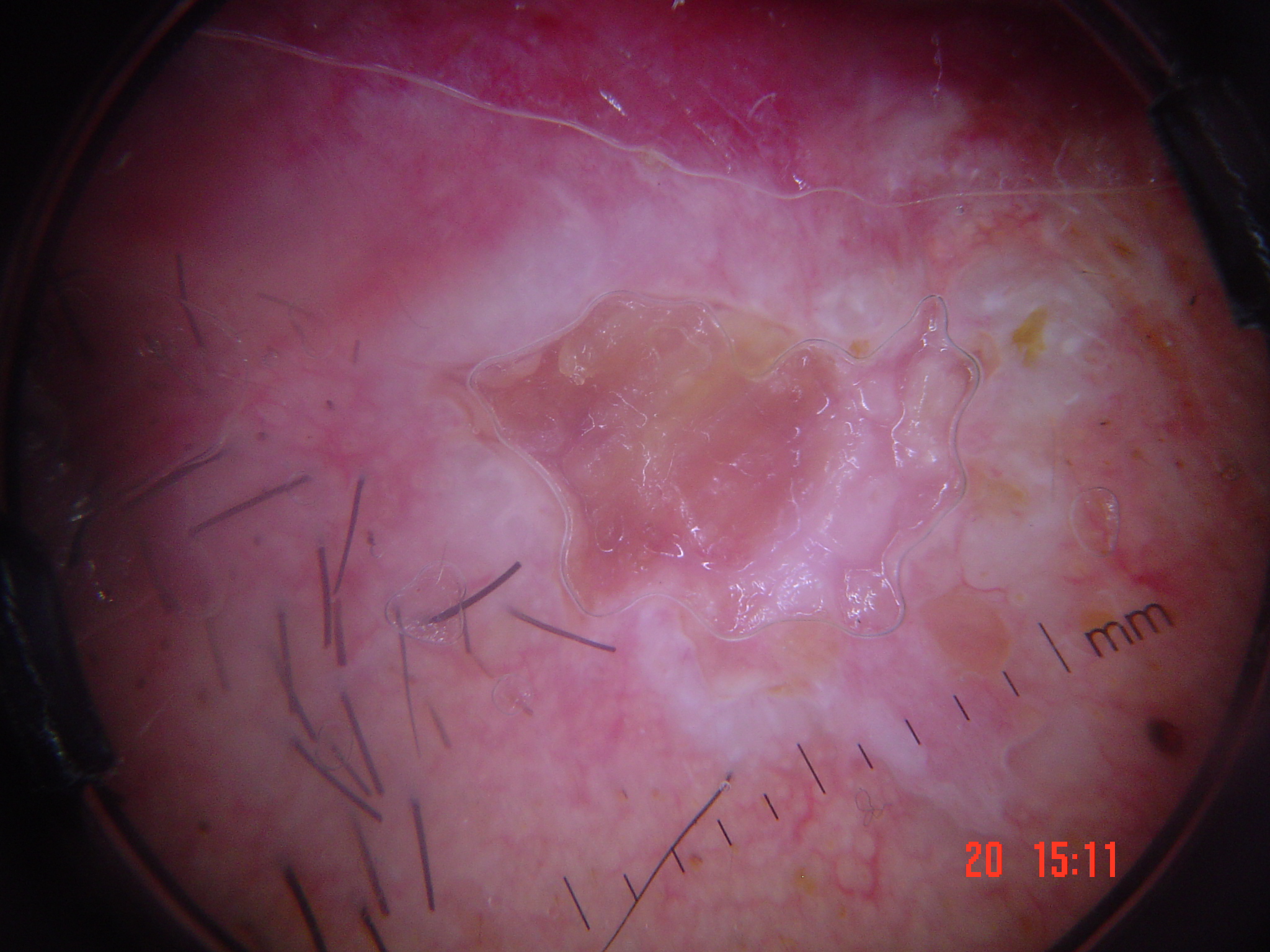A dermoscopic close-up of a skin lesion. The architecture is that of a keratinocytic lesion. The biopsy diagnosis was a malignancy — a squamous cell carcinoma.